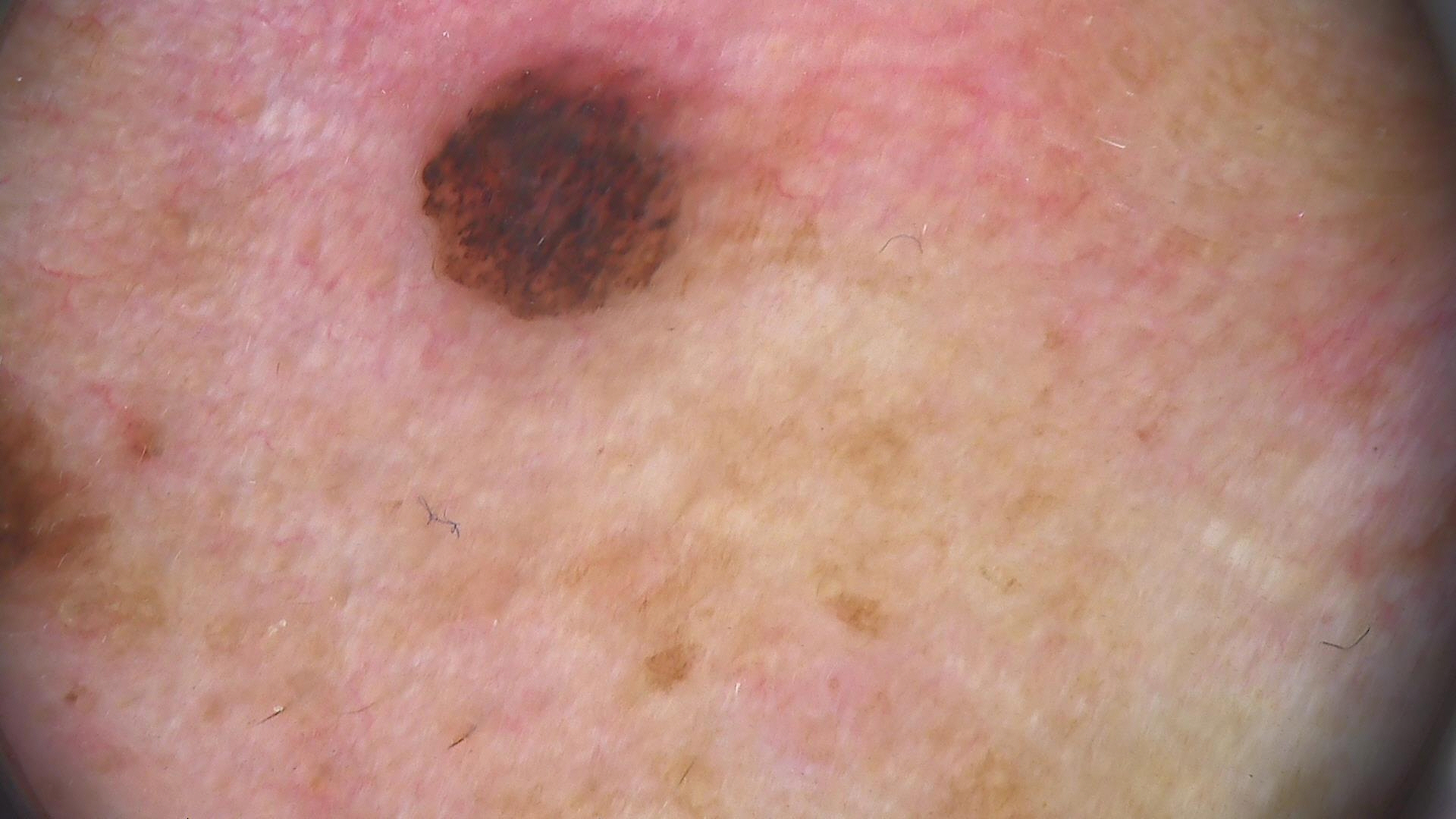Case:
A dermoscopy image of a single skin lesion.
Impression:
The diagnostic label was a compound nevus.